The affected area is the leg. Female contributor, age 30–39. The photo was captured at an angle:
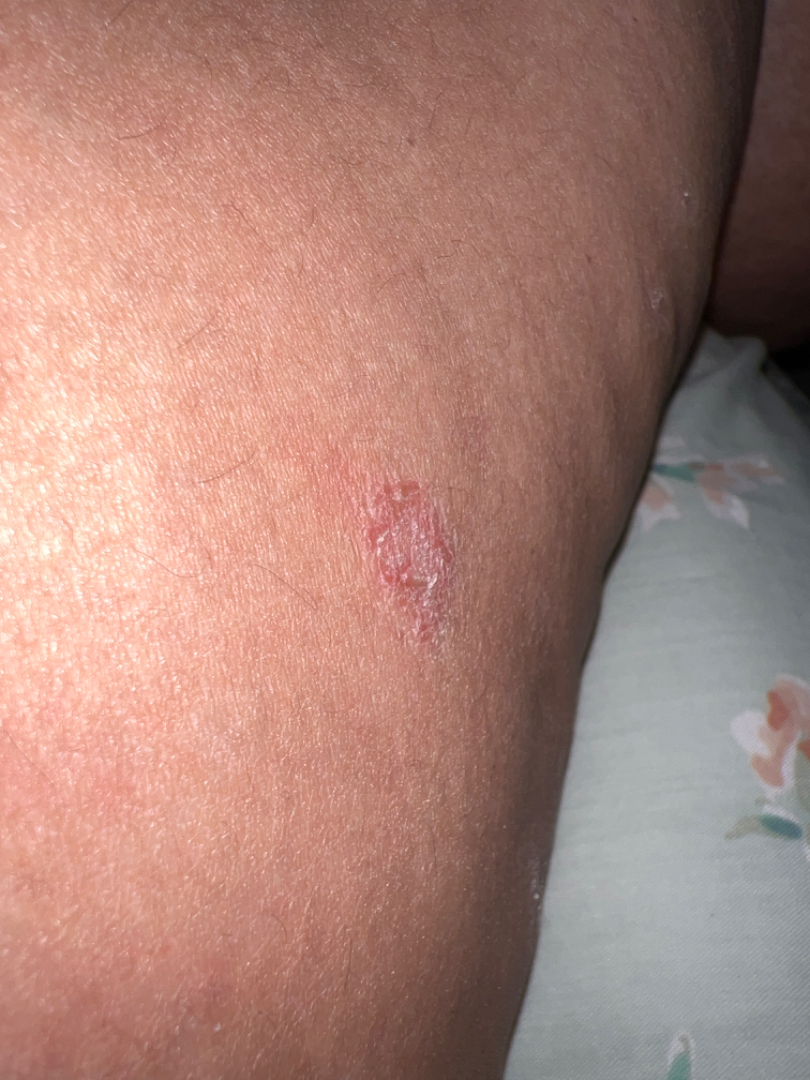Assessment:
On photographic review by a dermatologist: the leading impression is Porokeratosis; also raised was Actinic Keratosis; a remote consideration is SCC/SCCIS.